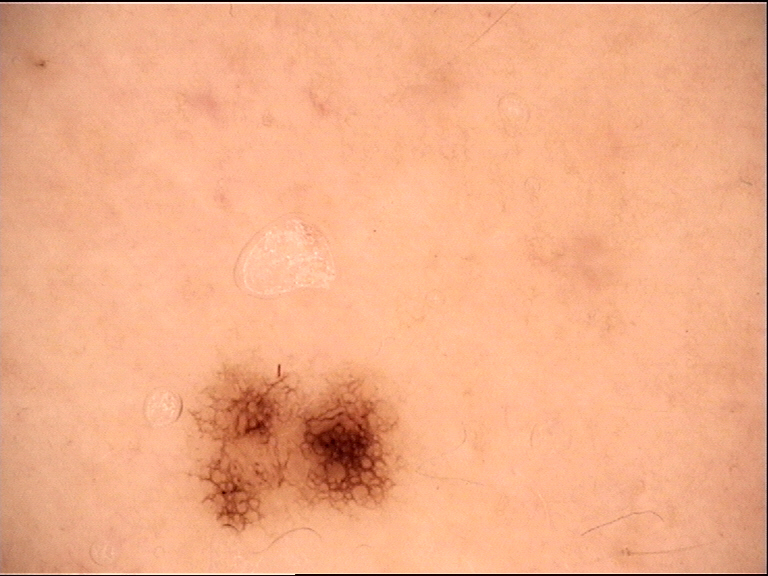imaging: dermoscopy; diagnostic label: dysplastic junctional nevus (expert consensus).